Located on the front of the torso · the photograph is a close-up of the affected area · the subject is 40–49, female:
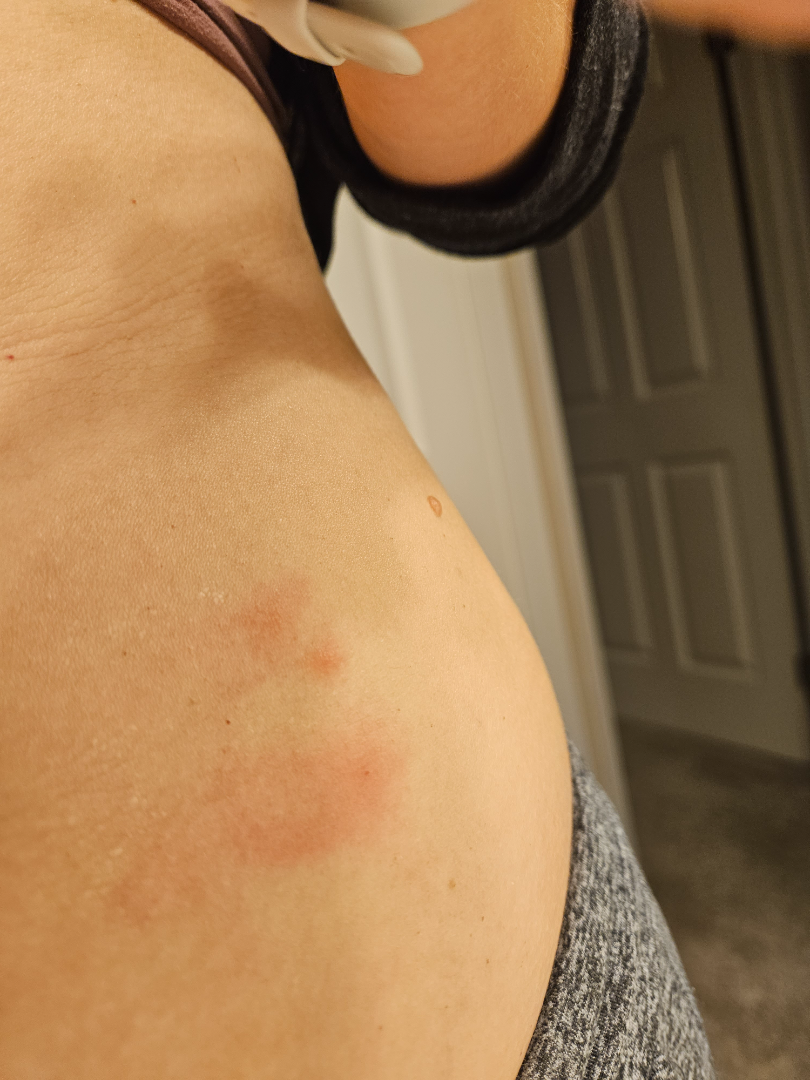The condition could not be reliably identified from the image.
The lesion is described as raised or bumpy.
Symptoms reported: itching.
The patient indicates the condition has been present for less than one week.
The patient considered this a rash.